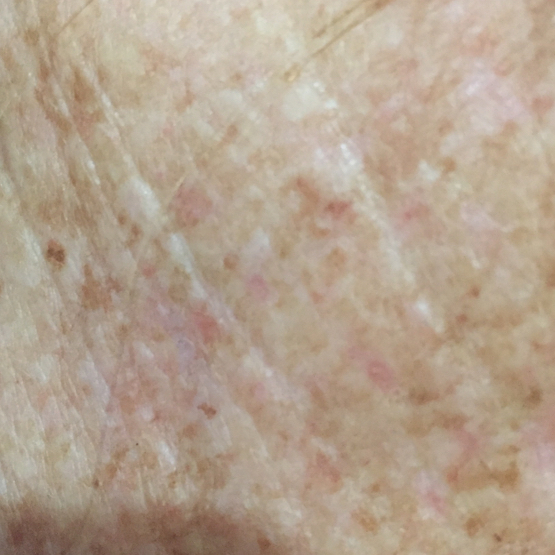subject: aged 50 | location: the chest | reported symptoms: none reported | diagnosis: actinic keratosis (clinical consensus).